The lesion is described as raised or bumpy; the patient described the issue as a rash; the contributor is 40–49, female; symptoms reported: itching, enlargement and burning; skin tone: FST IV; the lesion involves the leg and arm; the photo was captured at an angle.
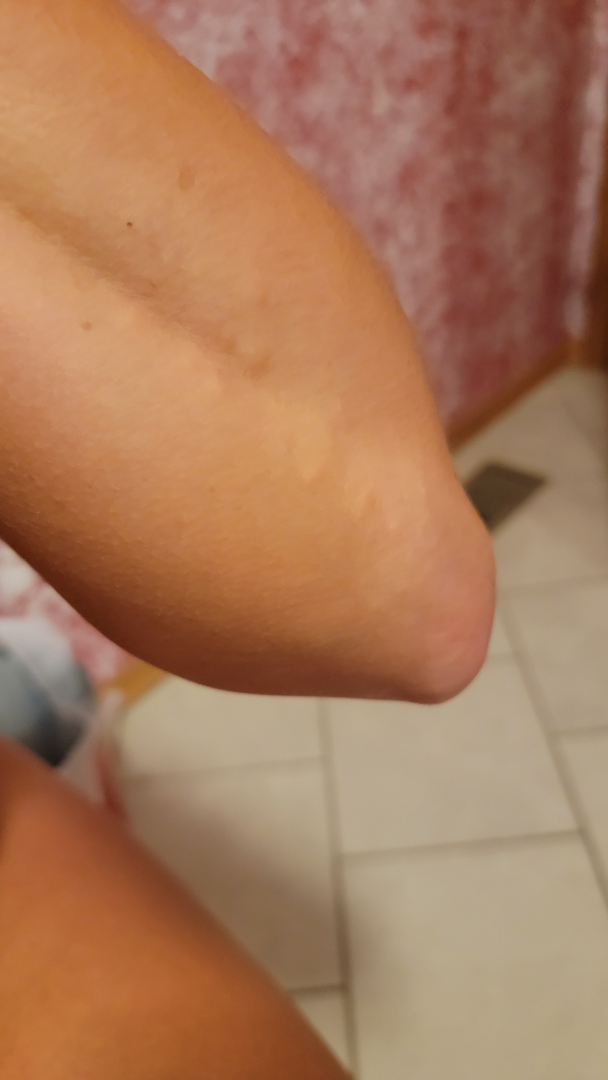The dermatologist found no clearly identifiable skin pathology in the image.